The photo was captured at a distance, located on the palm: 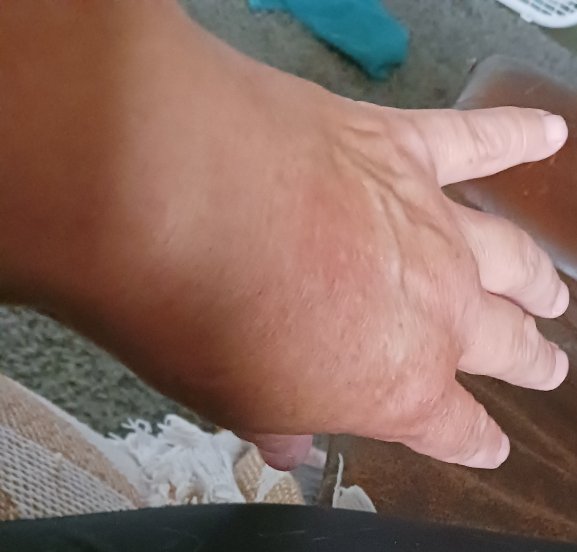Q: What was the assessment?
A: indeterminate from the photograph